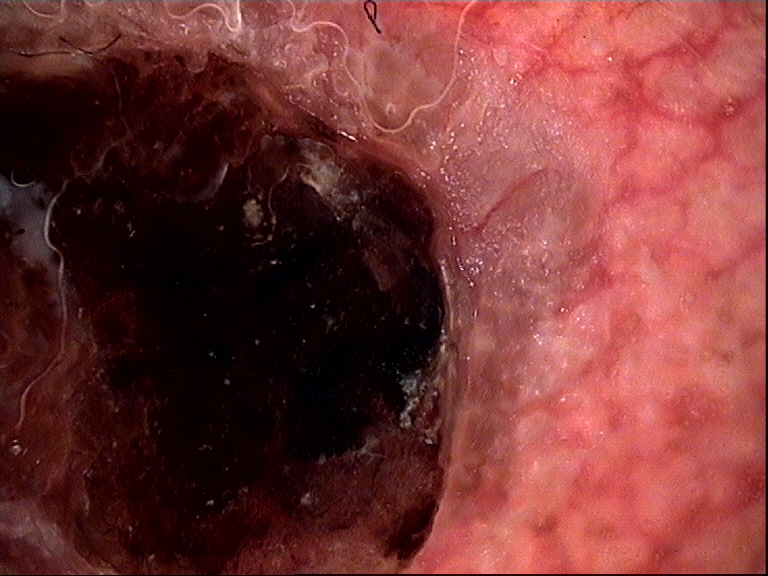Case:
Dermoscopy of a skin lesion.
Pathology:
The biopsy diagnosis was a keratinocytic lesion — a squamous cell carcinoma.